A dermoscopic close-up of a skin lesion · the subject is male — 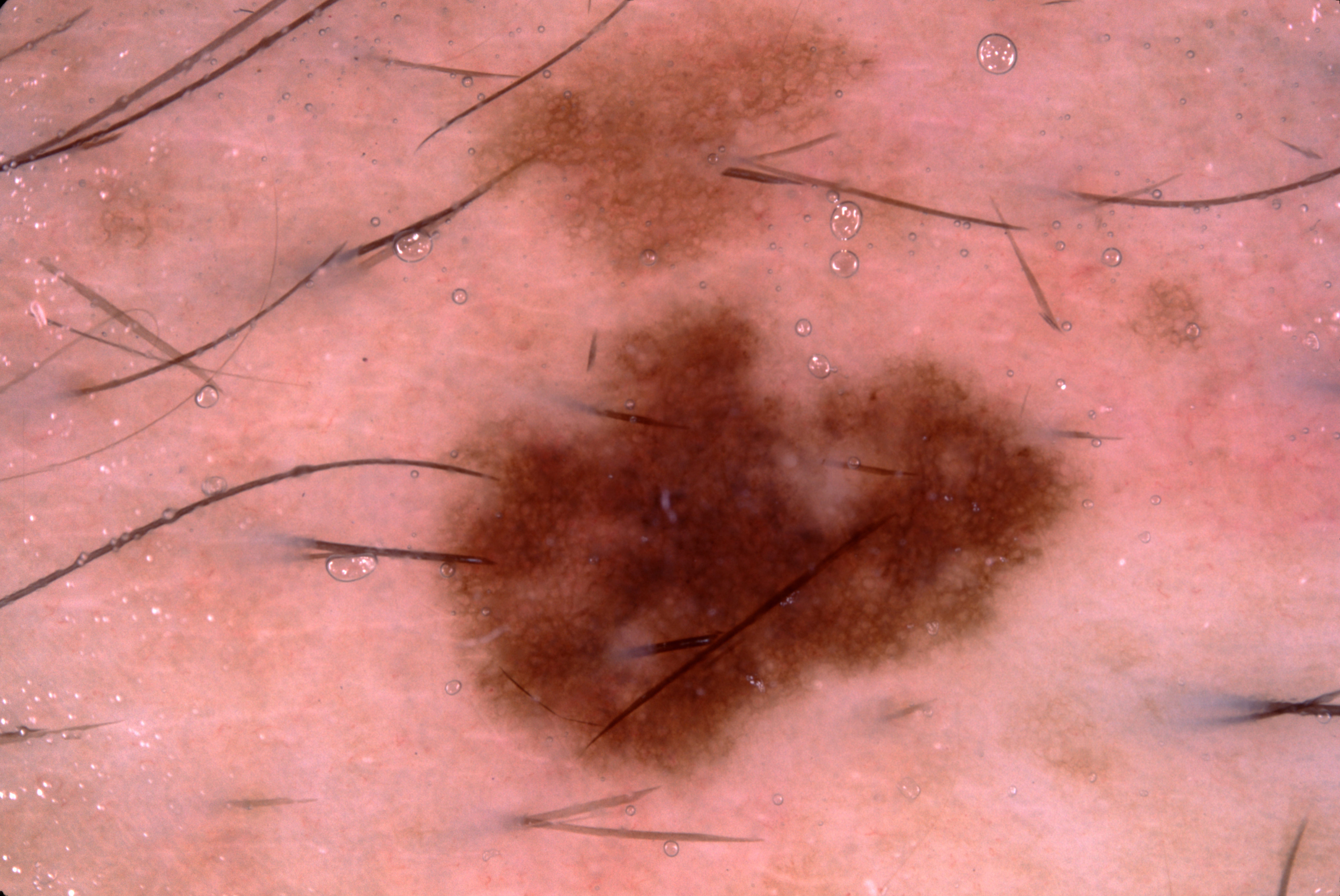The lesion occupies roughly 47% of the field. The lesion spans x1=347, y1=2, x2=1228, y2=824. Dermoscopic assessment notes pigment network. Diagnosed as a melanocytic nevus.